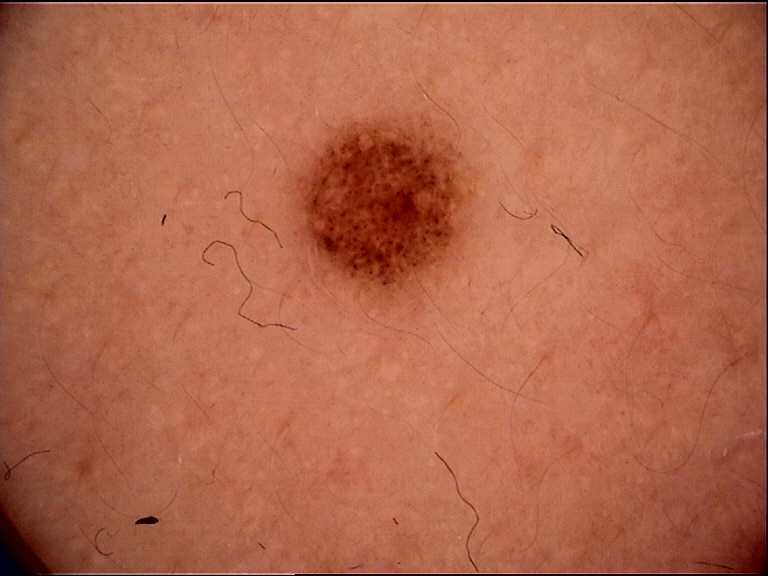diagnostic label: dysplastic junctional nevus (expert consensus)